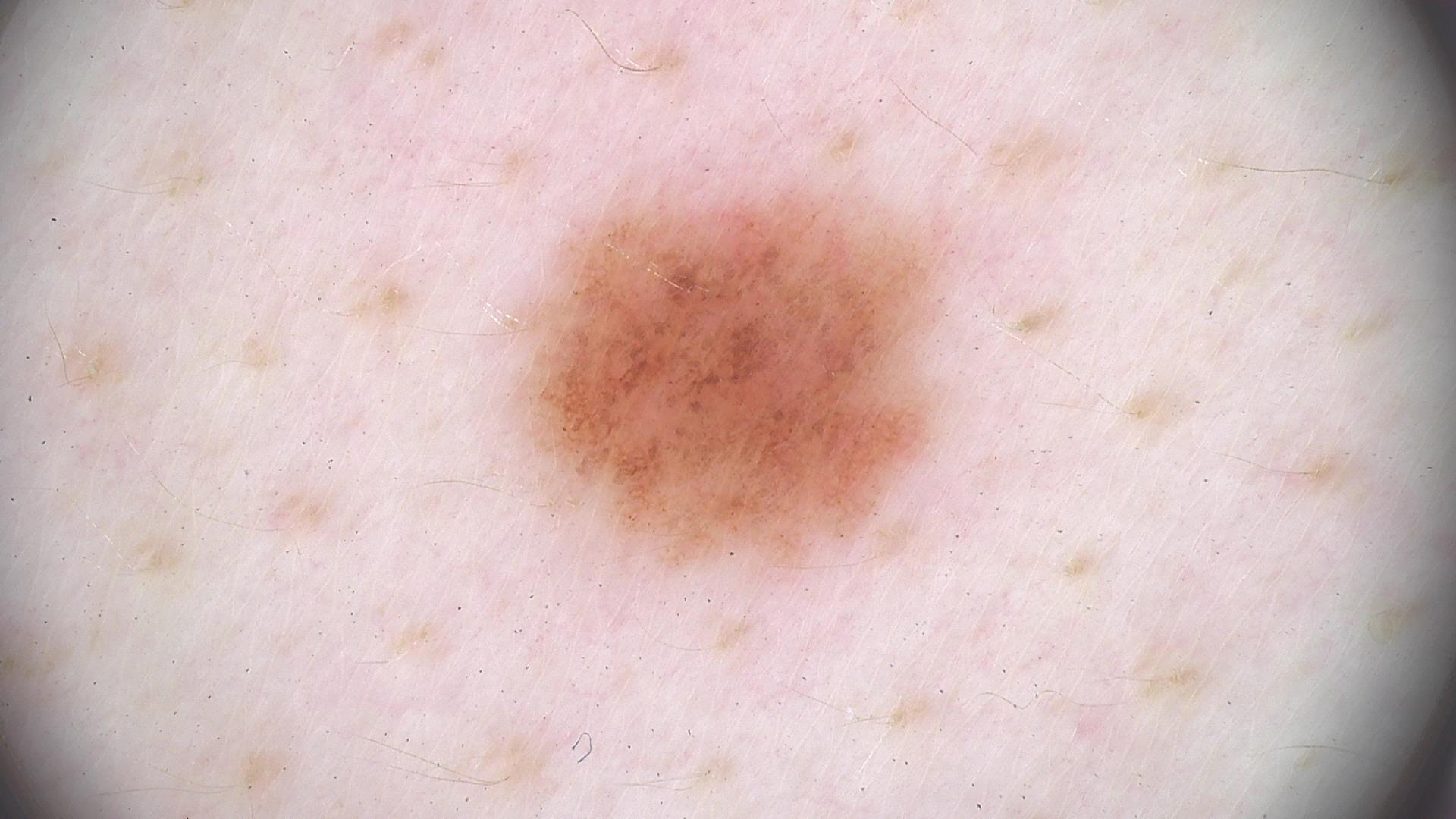Conclusion:
The diagnosis was a dysplastic junctional nevus.